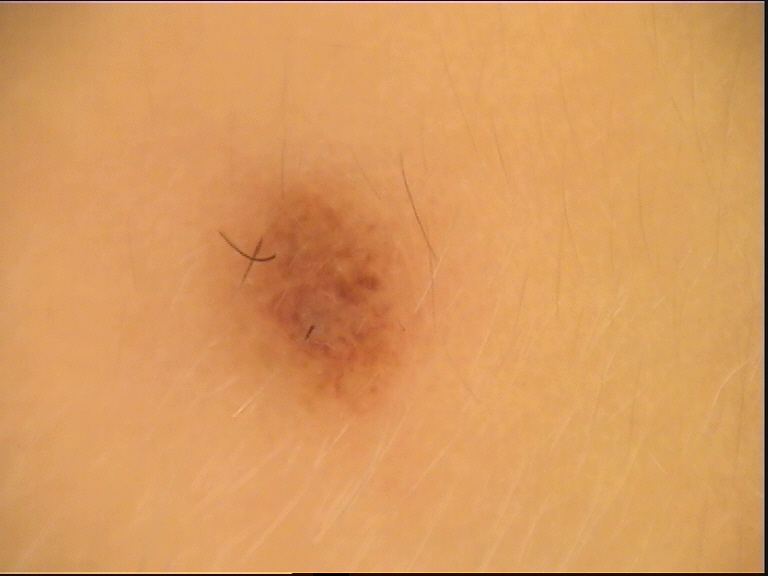Consistent with a compound nevus.